The subject is 50–59, female; the photograph was taken at an angle; located on the arm: 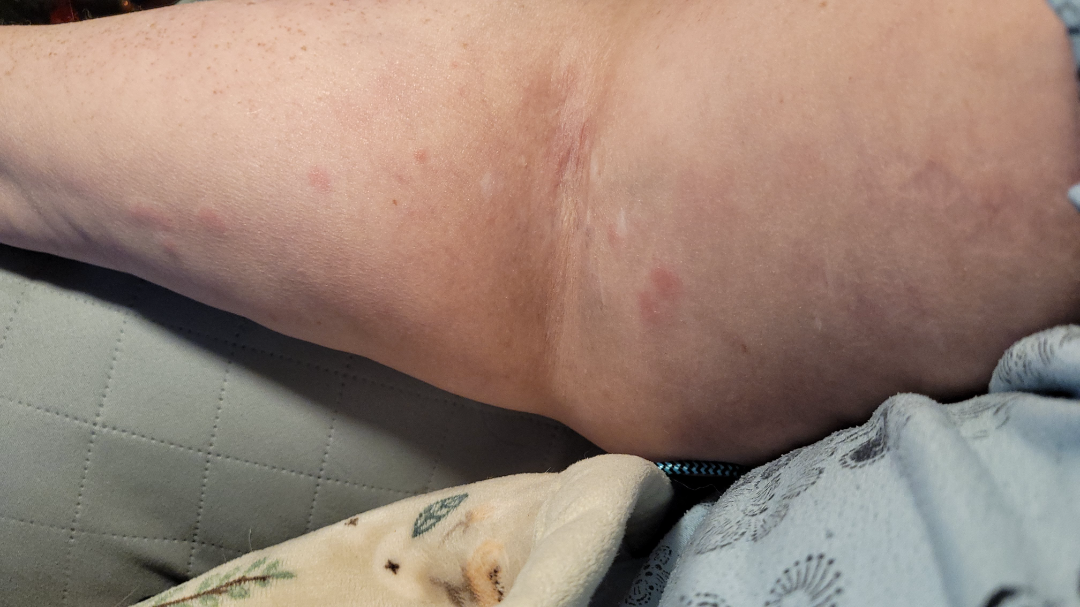{
  "differential": {
    "tied_lead": [
      "Eczema",
      "Allergic Contact Dermatitis",
      "Urticaria",
      "Insect Bite"
    ]
  }
}